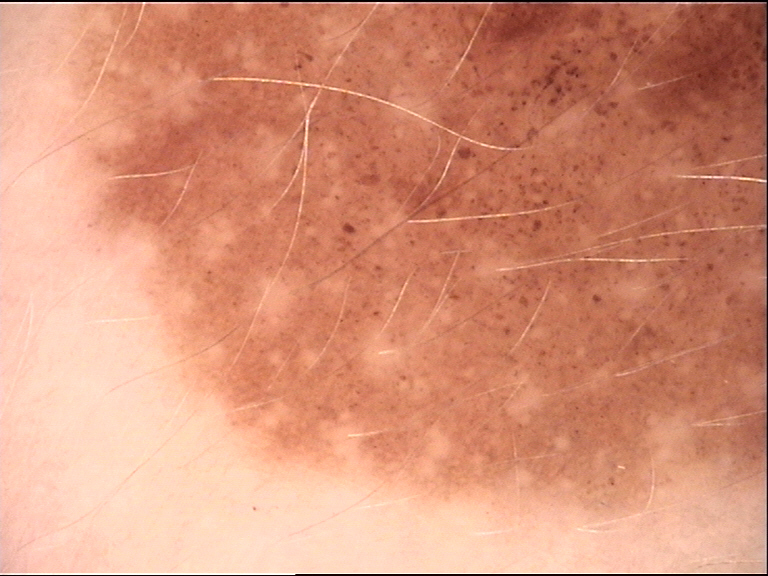Dermoscopy of a skin lesion. The diagnostic label was a banal lesion — a congenital junctional nevus.